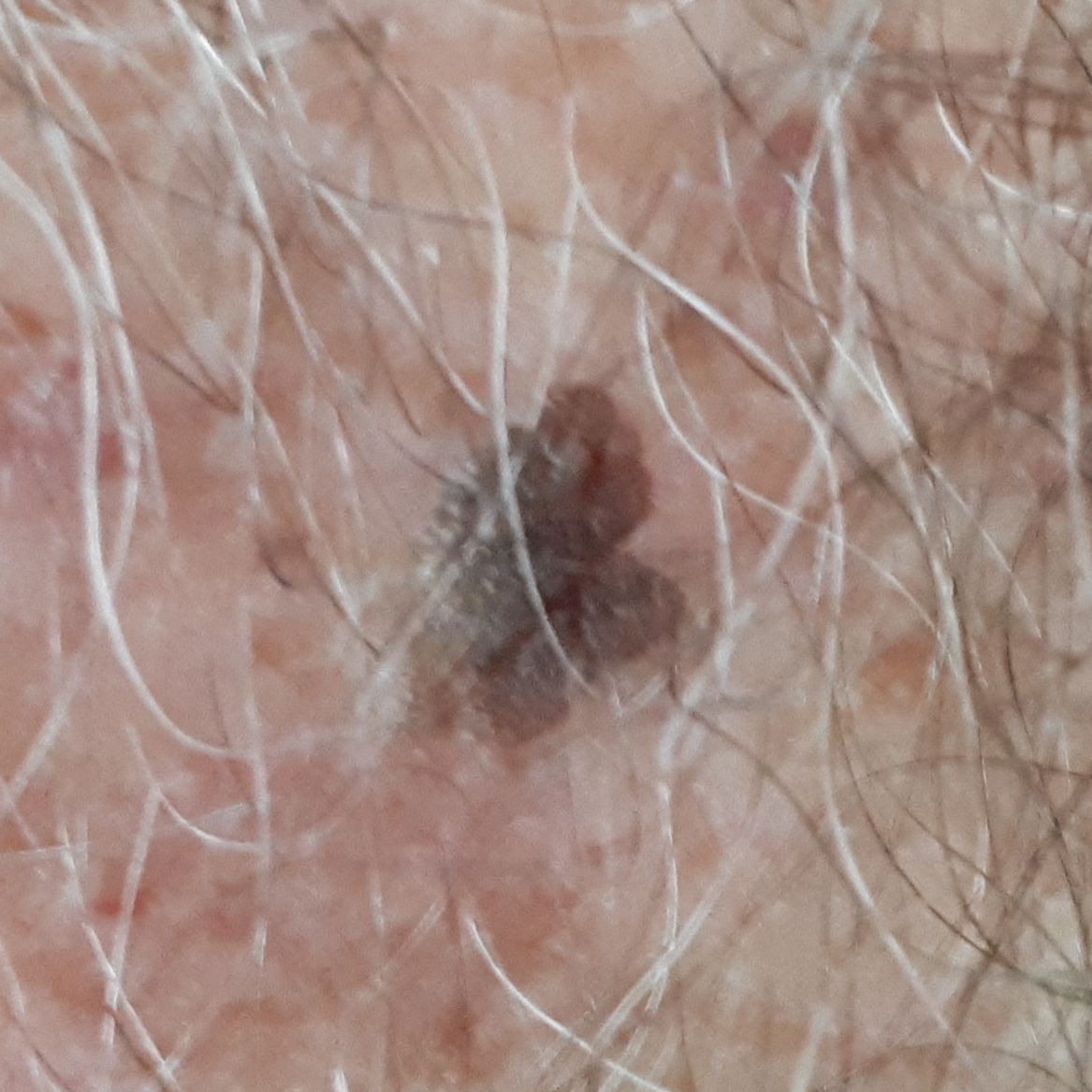A subject age 53. A clinical photograph showing a skin lesion. Diagnosed by dermatologist consensus as a seborrheic keratosis.